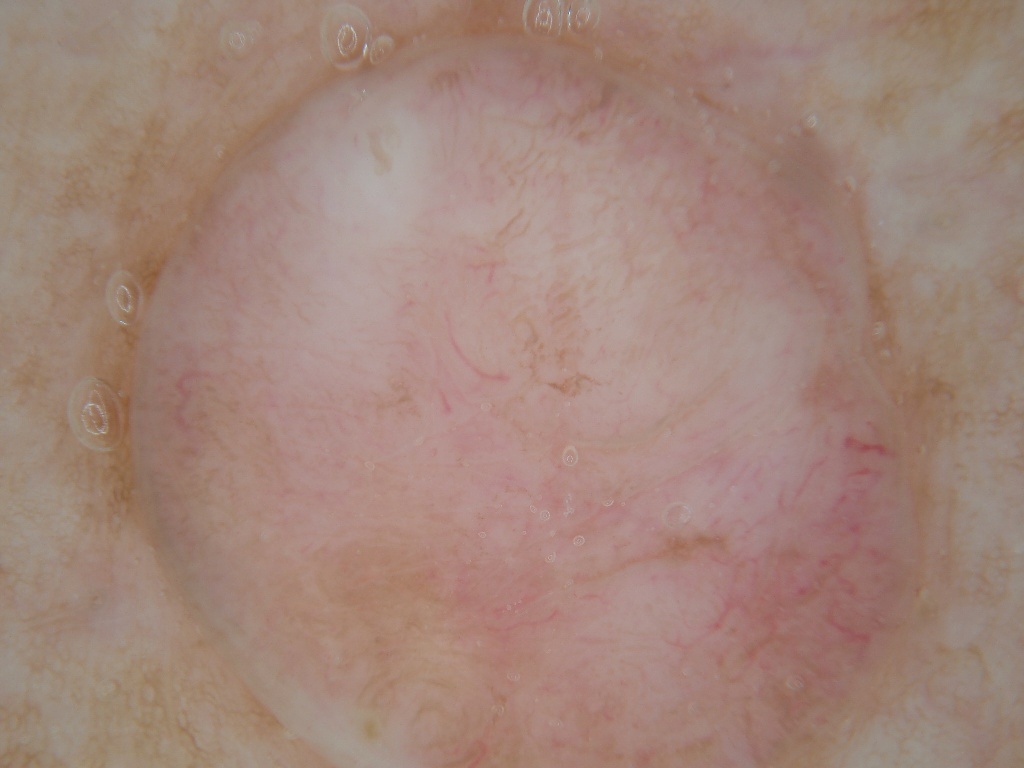Findings:
- image: dermoscopic image
- lesion extent: large
- bounding box: <box>129, 36, 927, 766</box>
- diagnosis: a benign lesion